A dermatoscopic image of a skin lesion: 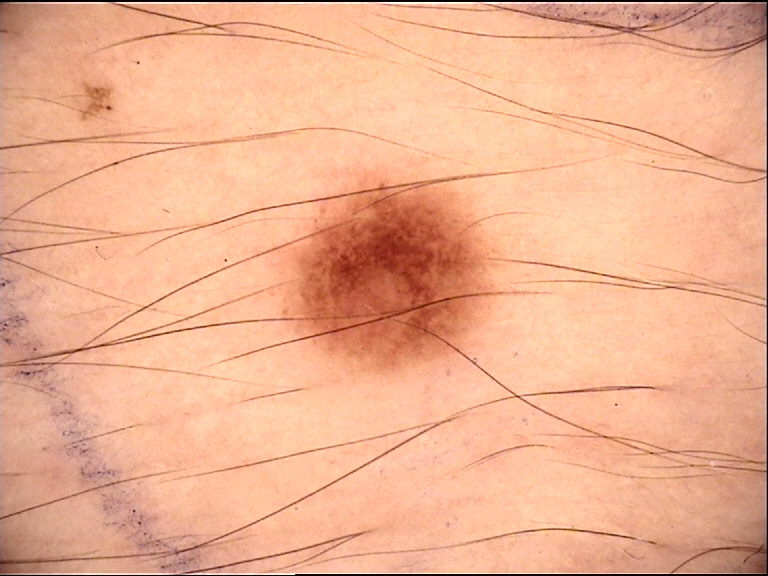The diagnostic label was a benign lesion — a dysplastic junctional nevus.